The subject is a female aged 18–29; Fitzpatrick phototype II; reported duration is less than one week; the lesion is described as raised or bumpy; an image taken at a distance; the affected area is the front of the torso, leg and back of the torso; the contributor notes itching and burning; the patient considered this skin that appeared healthy to them.
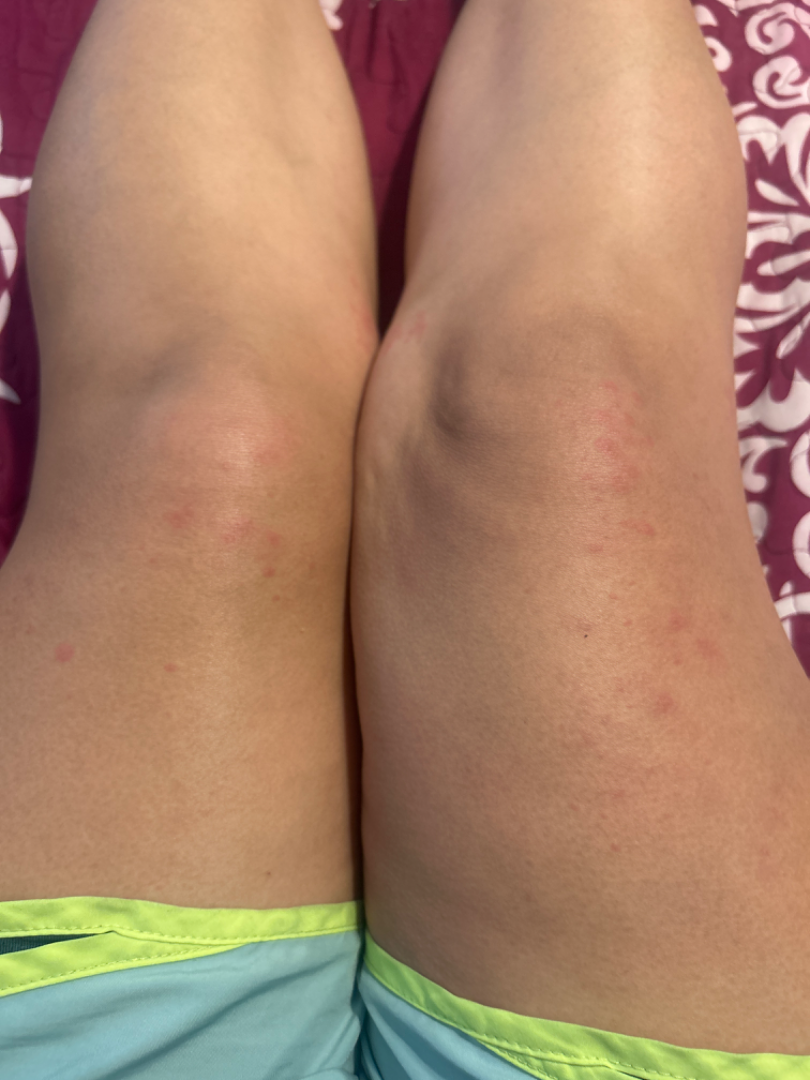Case summary:
• impression: Allergic Contact Dermatitis (primary); Eczema (remote); Dermatitis herpetiformis (remote); Insect Bite (remote); Folliculitis (remote)